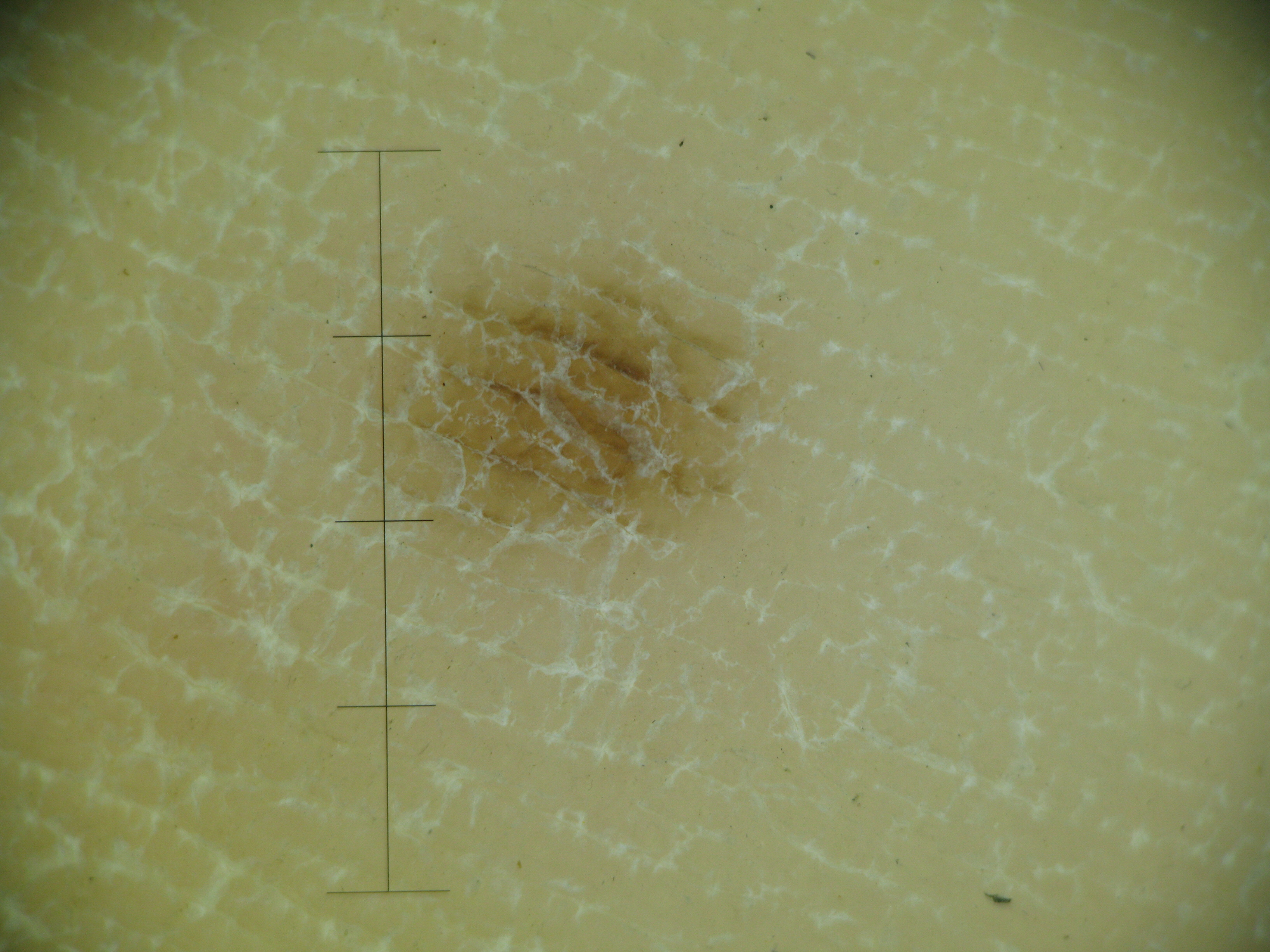diagnostic label: acral junctional nevus (expert consensus).